A skin lesion imaged with a dermatoscope.
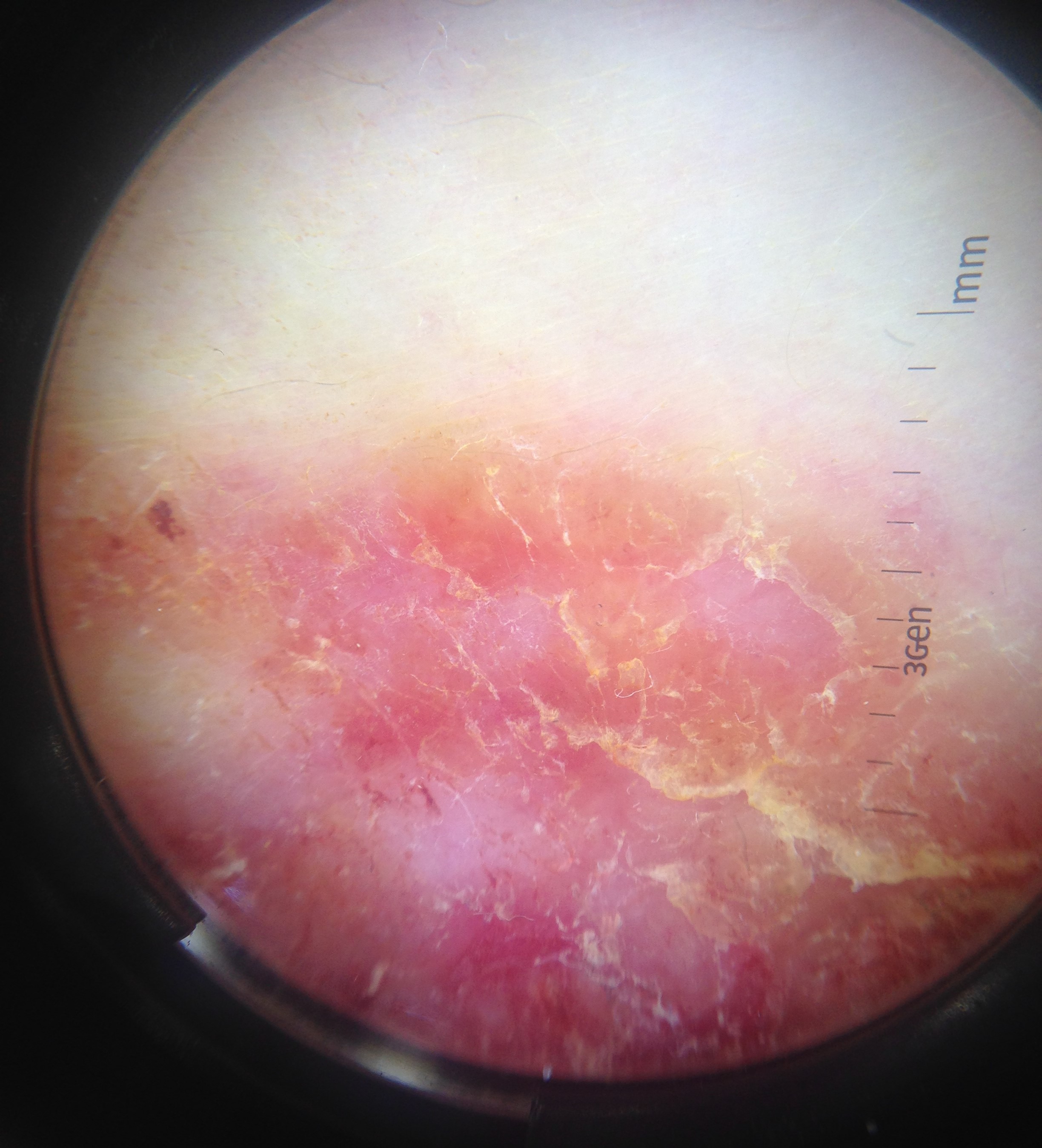Findings: This is a keratinocytic lesion. Pathology: The biopsy diagnosis was Bowen's disease.